The subject is 18–29, female · texture is reported as rough or flaky and raised or bumpy · close-up view · reported duration is one to four weeks · located on the head or neck · self-categorized by the patient as a rash:
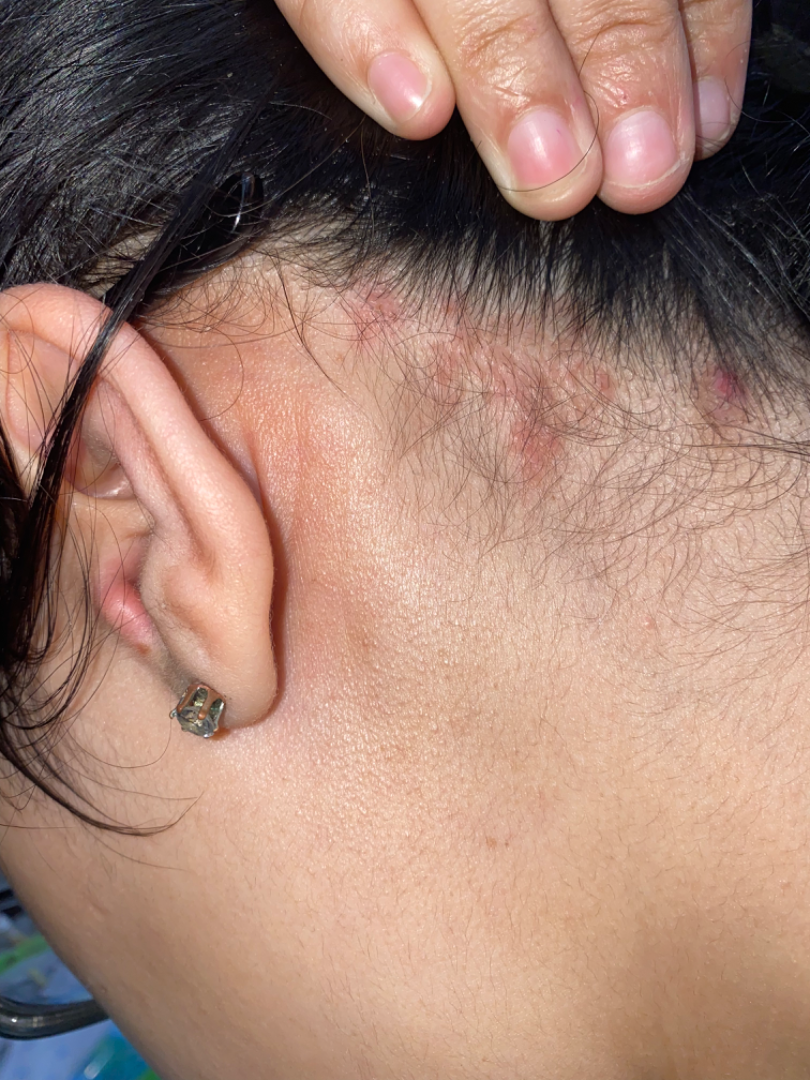Review: On remote review of the image: Folliculitis and Seborrheic Dermatitis were considered with similar weight.